The patient considered this a rash; reported duration is less than one week; the patient also reports joint pain; the lesion involves the arm, leg, front of the torso and back of the torso; the patient is female; reported lesion symptoms include bothersome appearance, itching and burning; this image was taken at a distance; skin tone: Fitzpatrick skin type III; the patient reports the lesion is raised or bumpy.
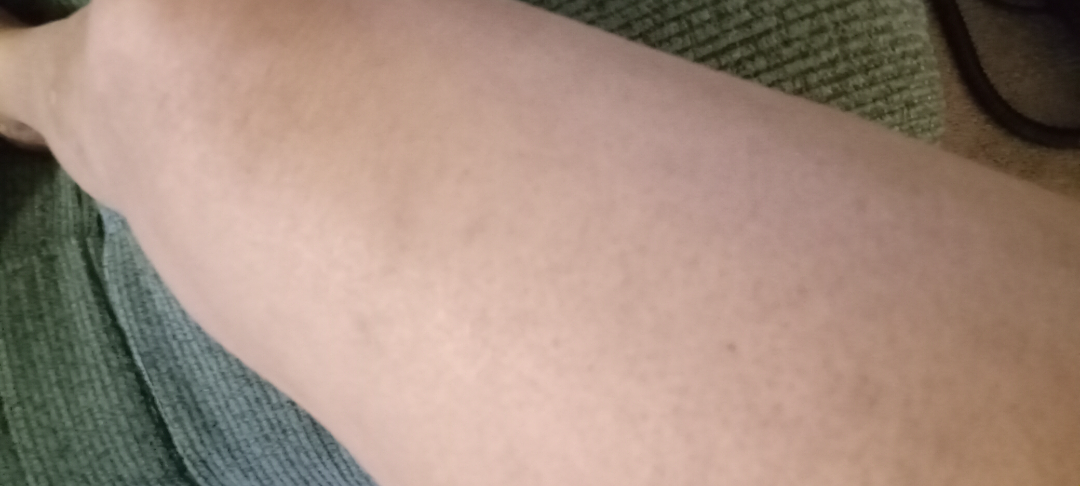Q: What was the assessment?
A: ungradable on photographic review